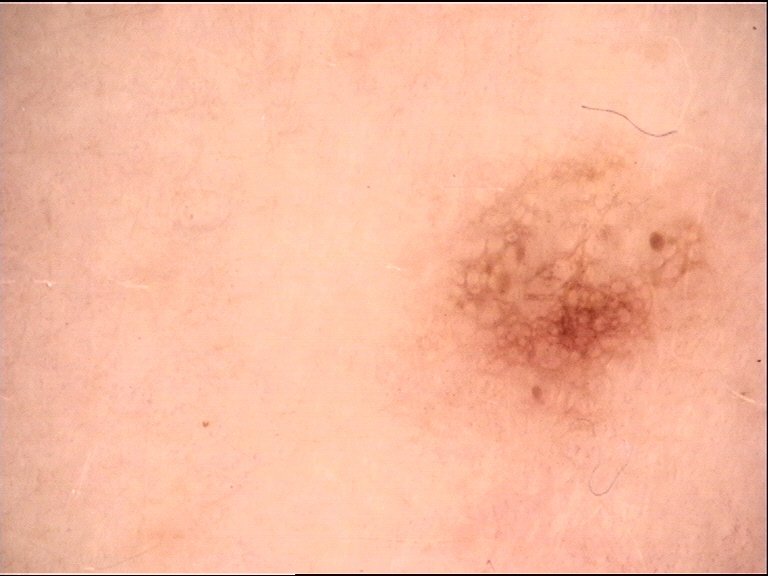| feature | finding |
|---|---|
| label | dysplastic junctional nevus (expert consensus) |